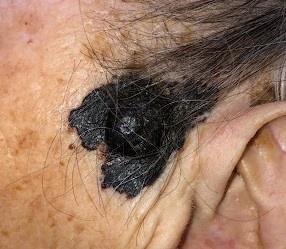A wide-field clinical photograph of a skin lesion. A female patient aged 83 or older. The lesion is on the head or neck. Biopsy-confirmed as a melanoma.